A dermoscopy image of a single skin lesion.
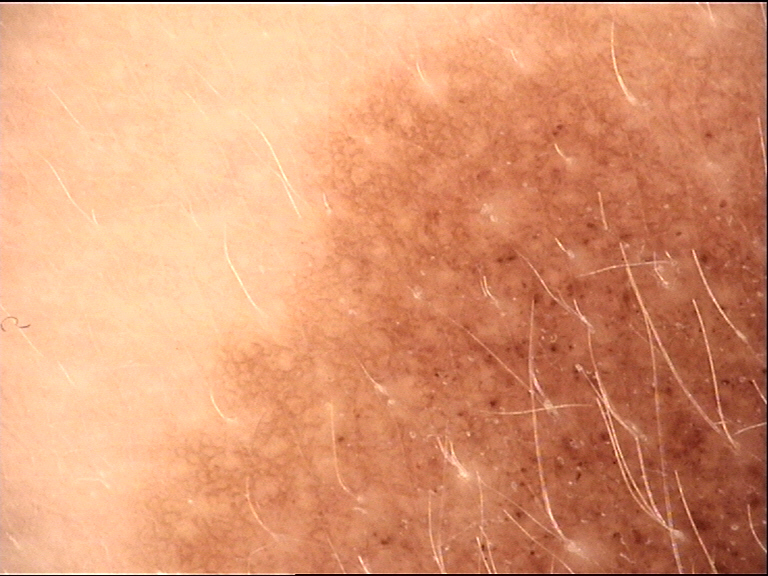Q: What was the diagnostic impression?
A: congenital compound nevus (expert consensus)